A dermoscopy image of a single skin lesion:
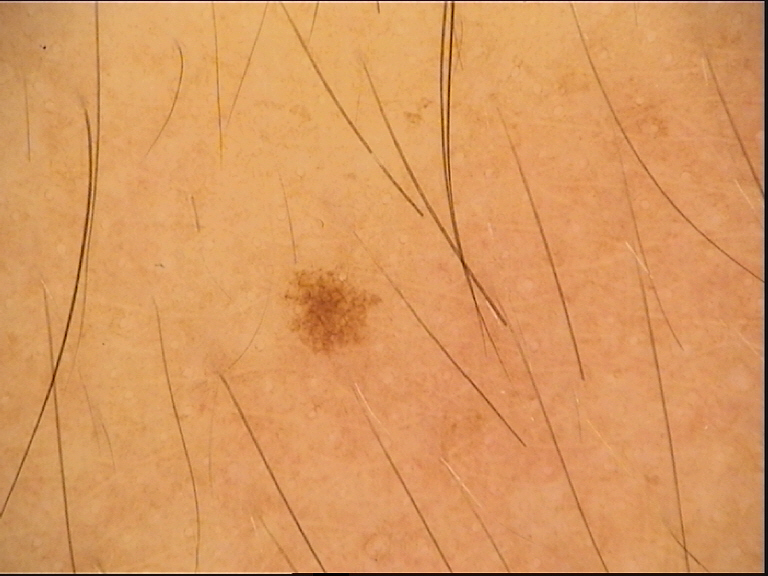Conclusion: The diagnosis was a benign lesion — a dysplastic junctional nevus.